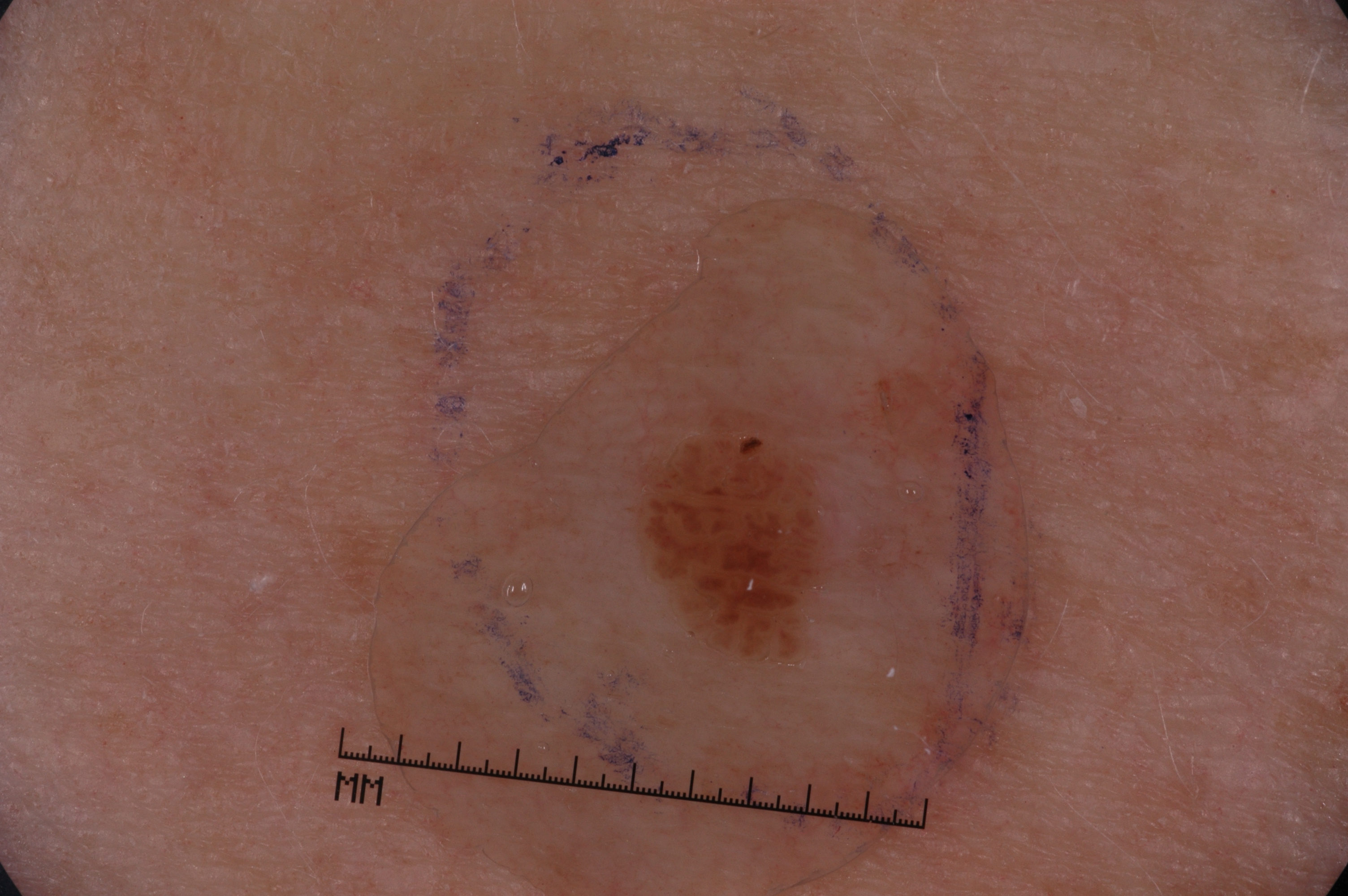Case summary:
A dermatoscopic image of a skin lesion. A female subject roughly 60 years of age. As (left, top, right, bottom), the lesion is bounded by [630, 401, 844, 677]. The lesion is small relative to the field of view. Dermoscopy demonstrates milia-like cysts.
Impression:
Expert review diagnosed this as a seborrheic keratosis.